A skin lesion imaged with a dermatoscope · acquired for a research image collection, with no referral diagnosis: 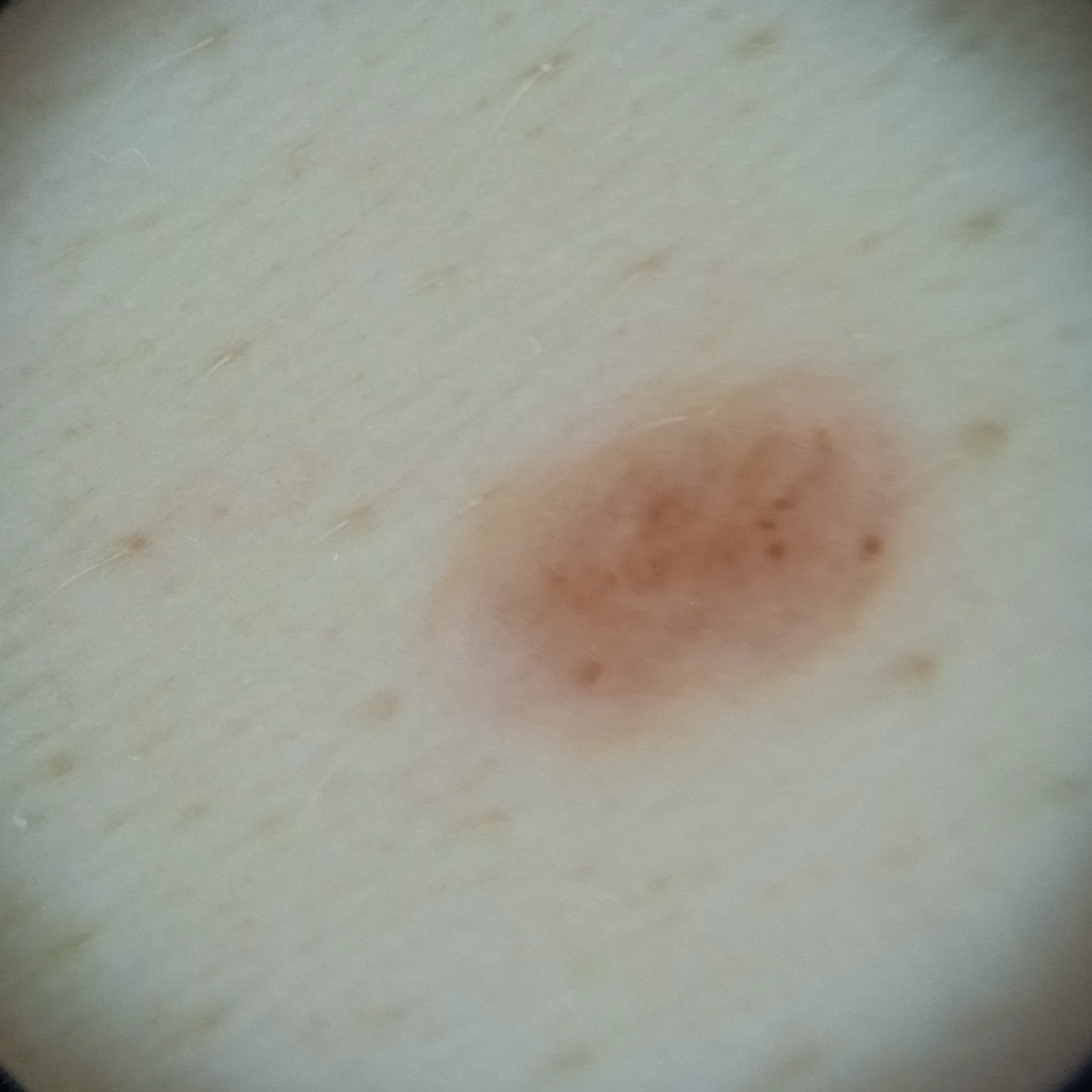The lesion measures approximately 4.9 mm.
The lesion was assessed as a melanocytic nevus.